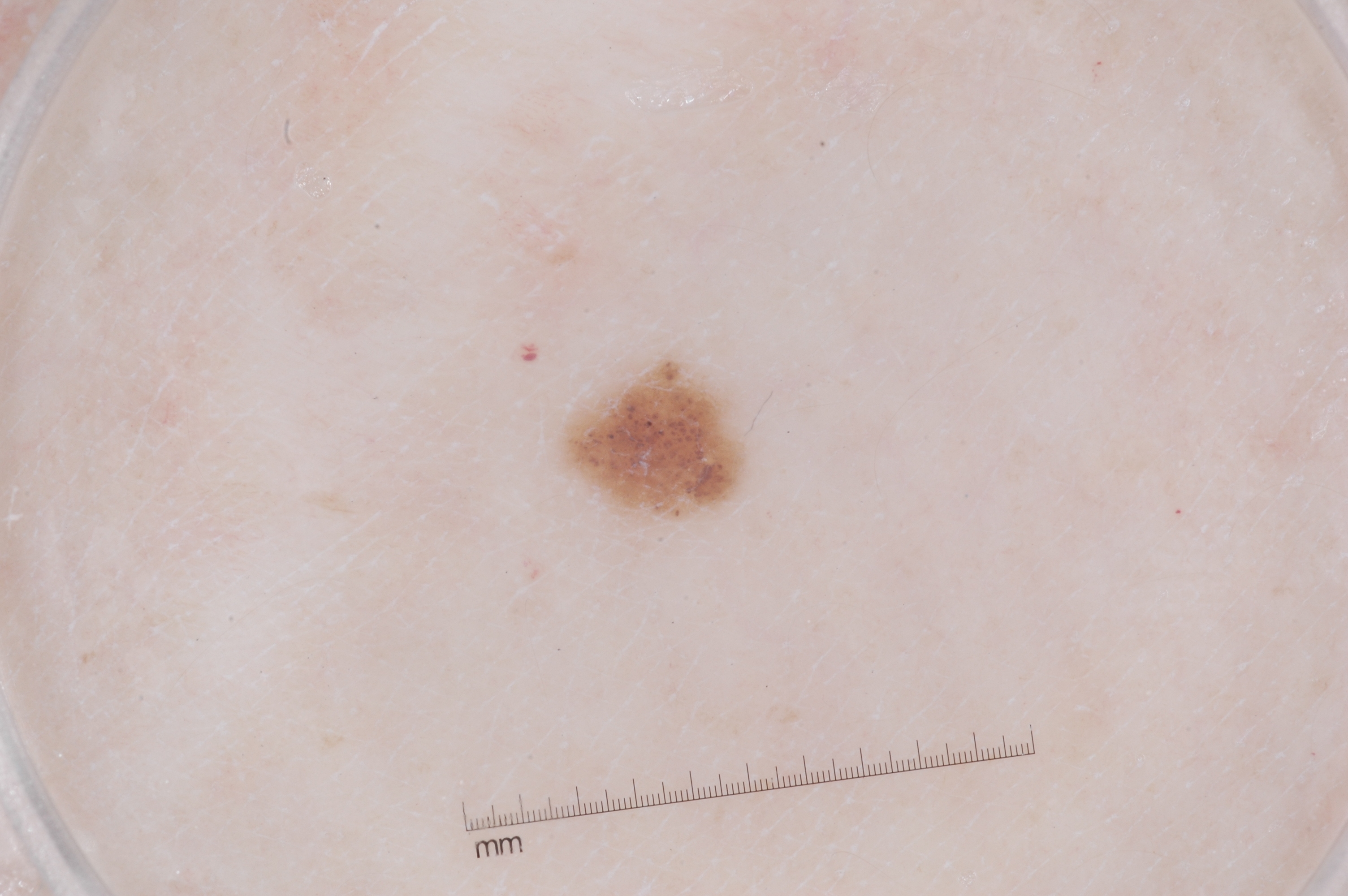| key | value |
|---|---|
| image type | dermatoscopic image of a skin lesion |
| dermoscopic findings | milia-like cysts; absent: negative network, pigment network, and streaks |
| lesion bbox | [569, 364, 747, 525] |
| impression | a melanocytic nevus, a benign skin lesion |